Dermoscopy of a skin lesion:
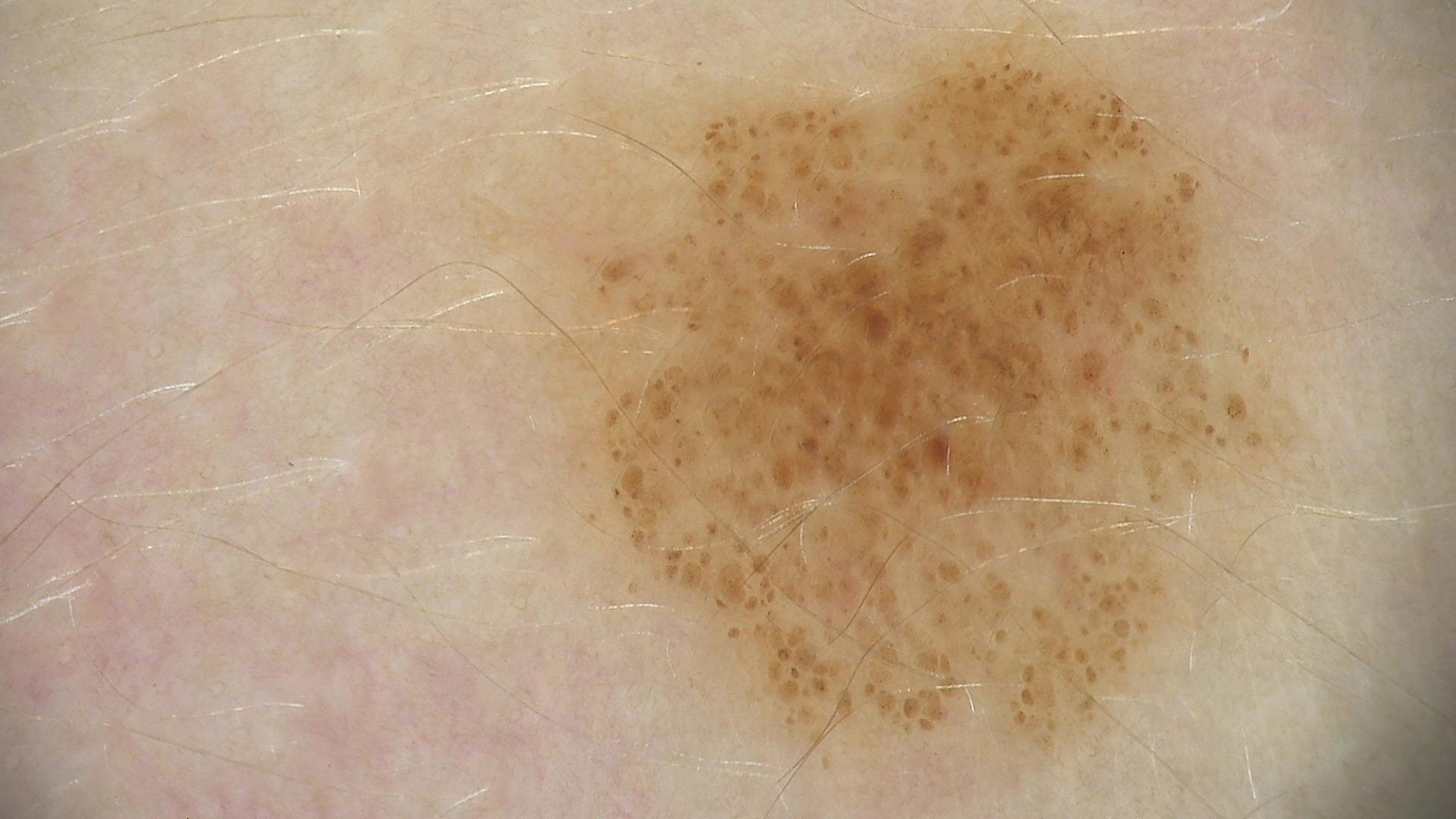assessment = dysplastic junctional nevus (expert consensus)